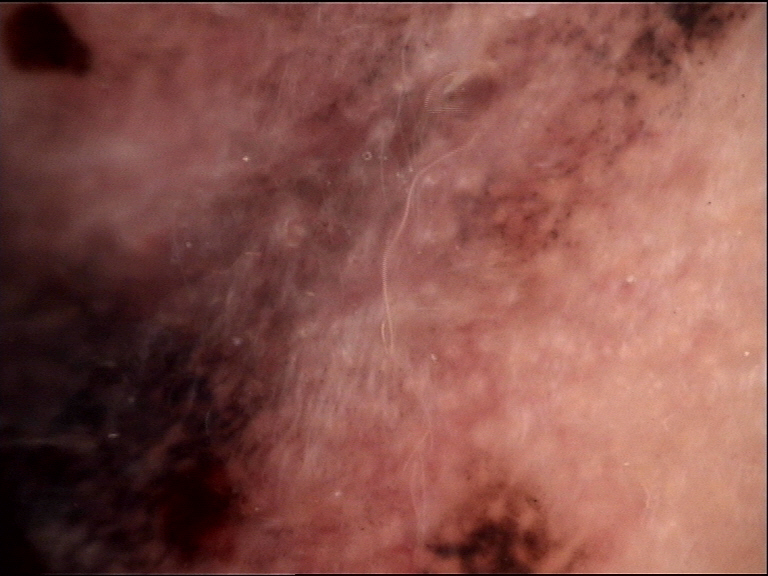Q: What is this lesion?
A: lentigo maligna (biopsy-proven)